A clinical photograph showing a skin lesion · a subject age 65: 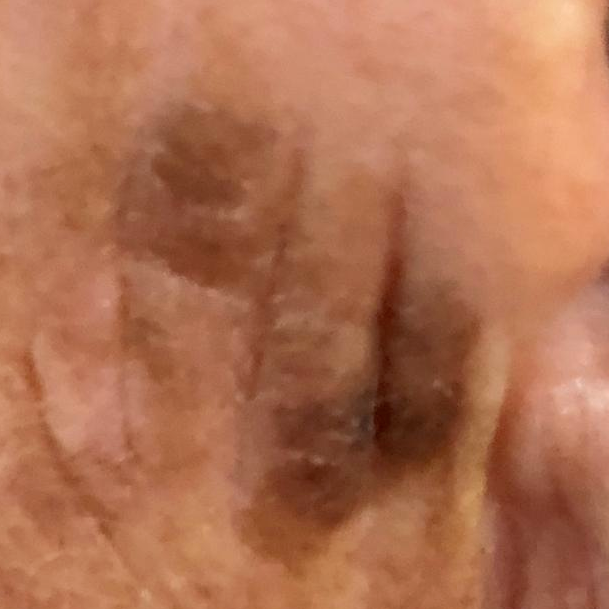Case:
– location: an ear
– patient-reported symptoms: none reported
– impression: seborrheic keratosis (clinical consensus)